FST IV; non-clinician graders estimated Monk skin tone scale 2–3. This is a close-up image — 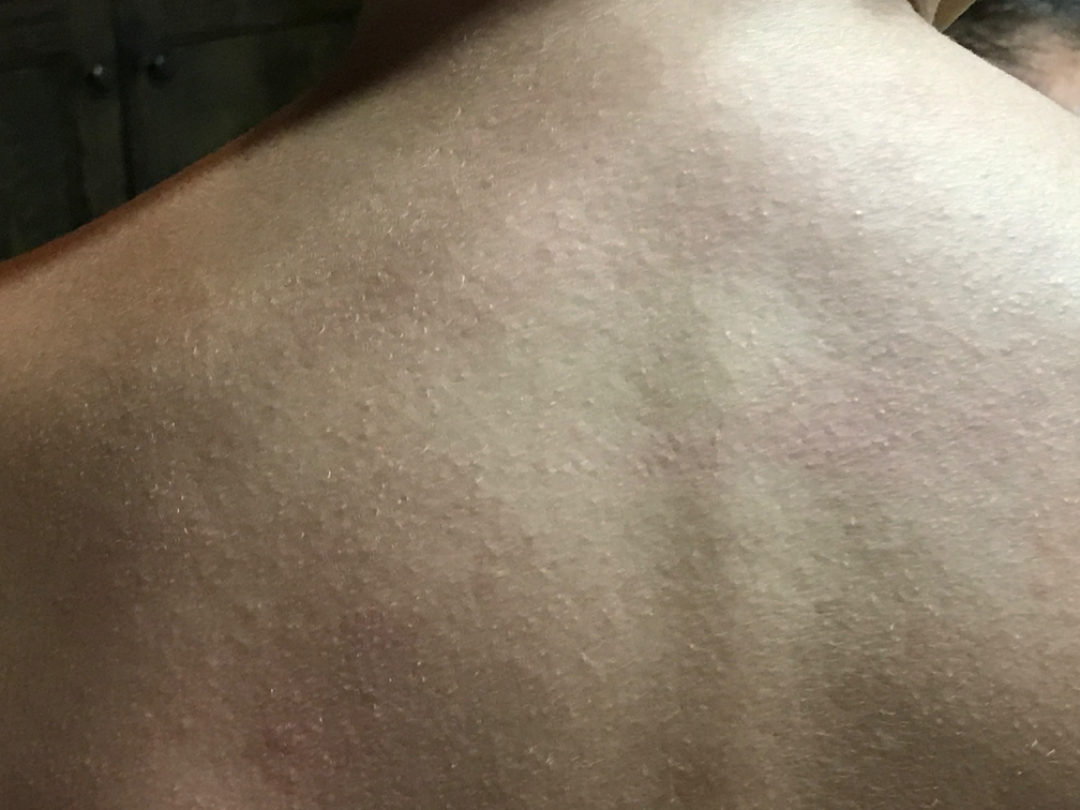Single-reviewer assessment: in keeping with Miliaria.